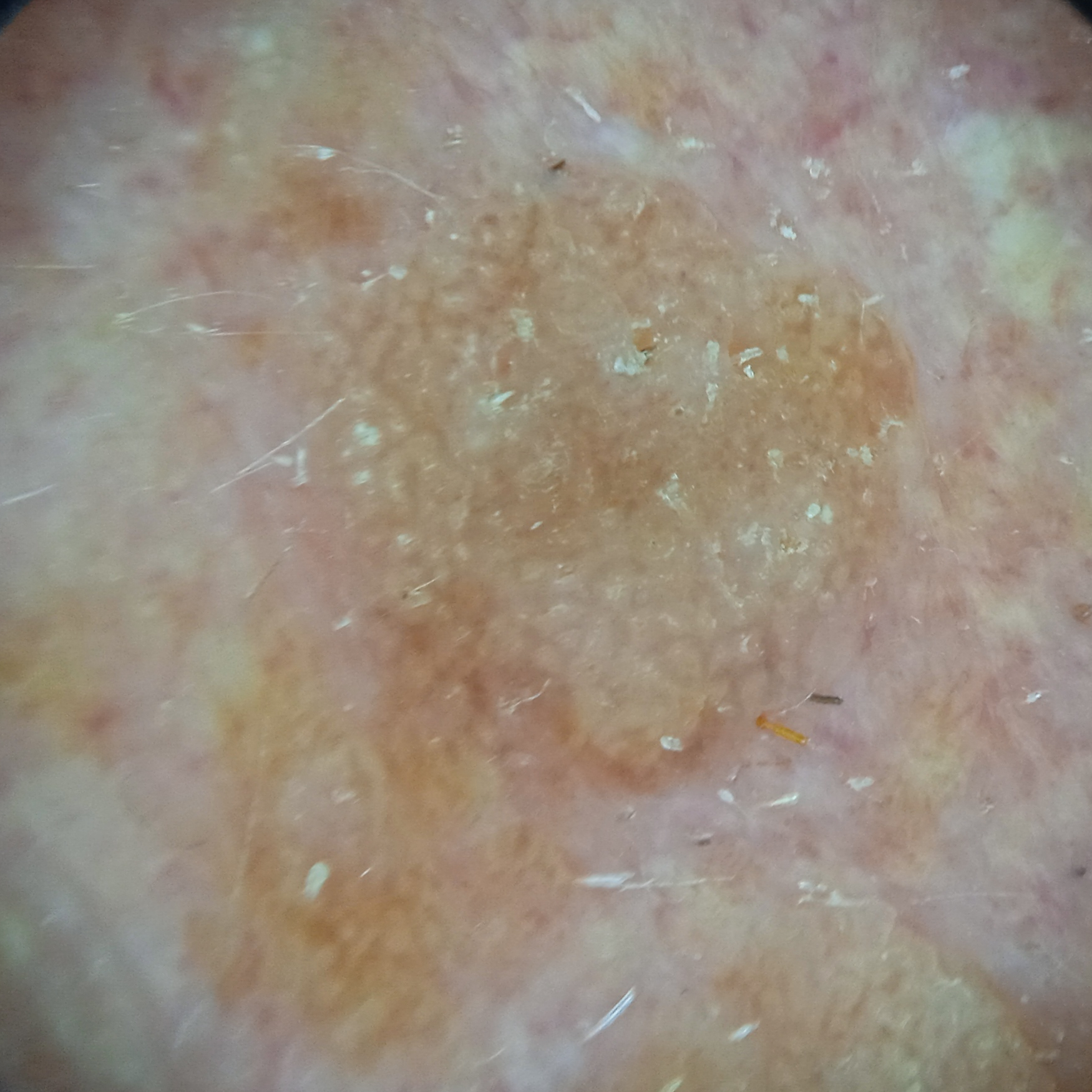subject — male, aged 62; size — 7.5 mm; diagnostic label — seborrheic keratosis (dermatologist consensus).